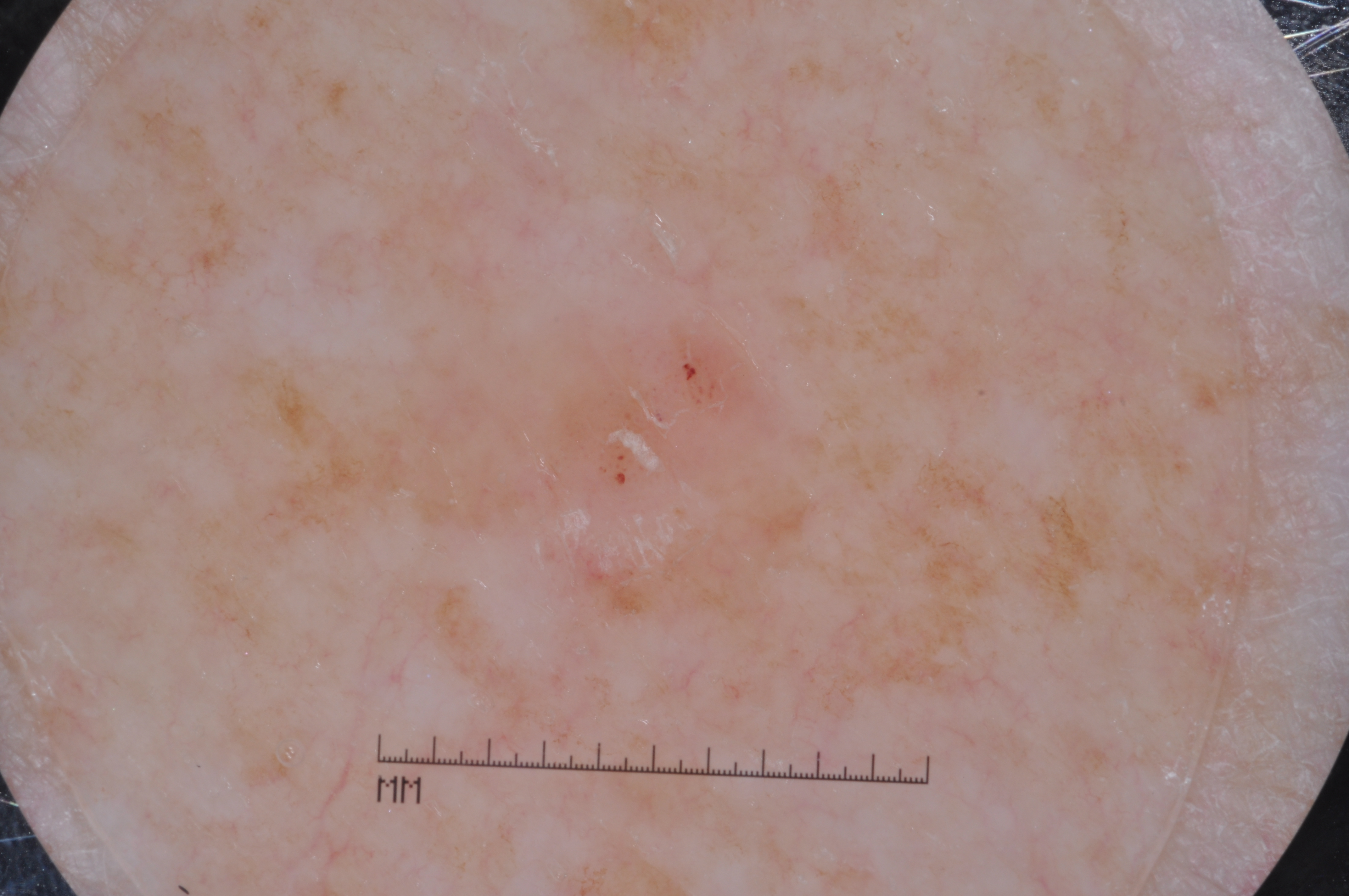patient = female, about 65 years old
image type = dermoscopic image
bounding box = box(443, 305, 824, 605)
size = ~7% of the field
dermoscopic features not present = milia-like cysts, pigment network, negative network, and streaks
diagnosis = a seborrheic keratosis, a non-melanocytic (keratinocytic) lesion